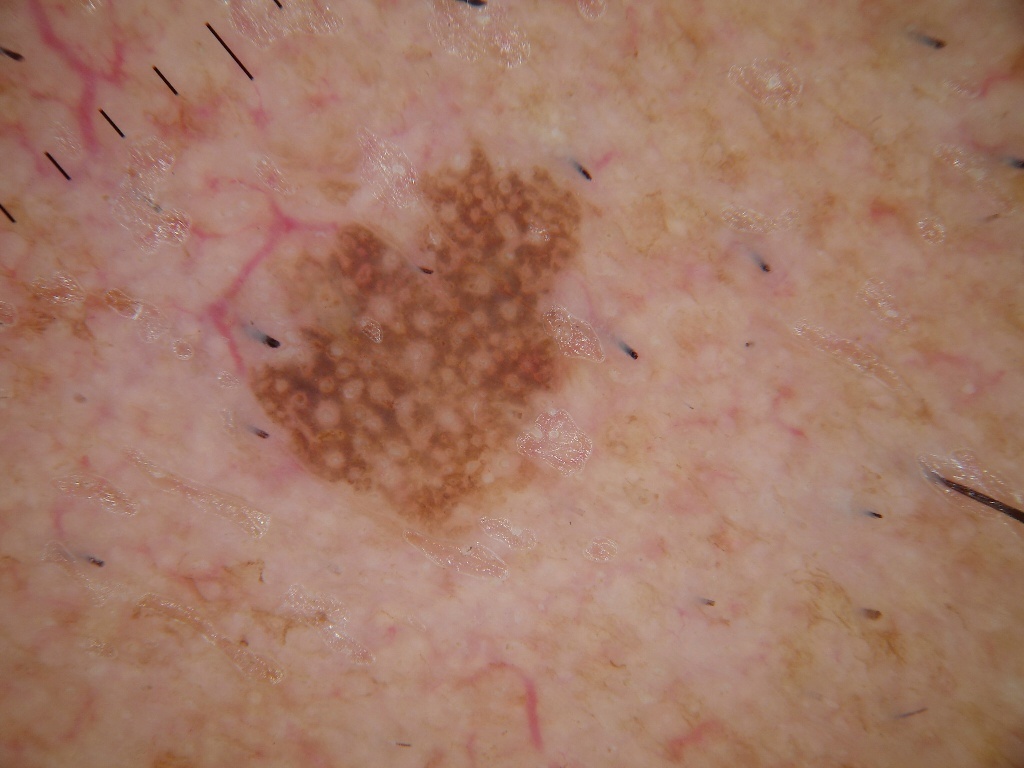A dermoscopic image of a skin lesion.
On dermoscopy, the lesion shows neither globules nor streaks.
The lesion's extent is 232, 120, 604, 552.
The lesion takes up a moderate portion of the field.
Clinically diagnosed as a benign skin lesion.